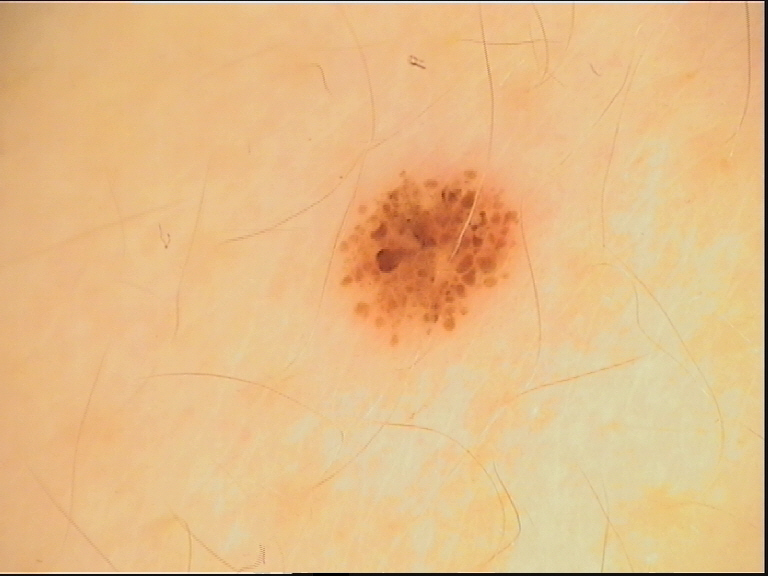label: dysplastic junctional nevus (expert consensus).